Acquired for a research image collection, with no referral diagnosis — 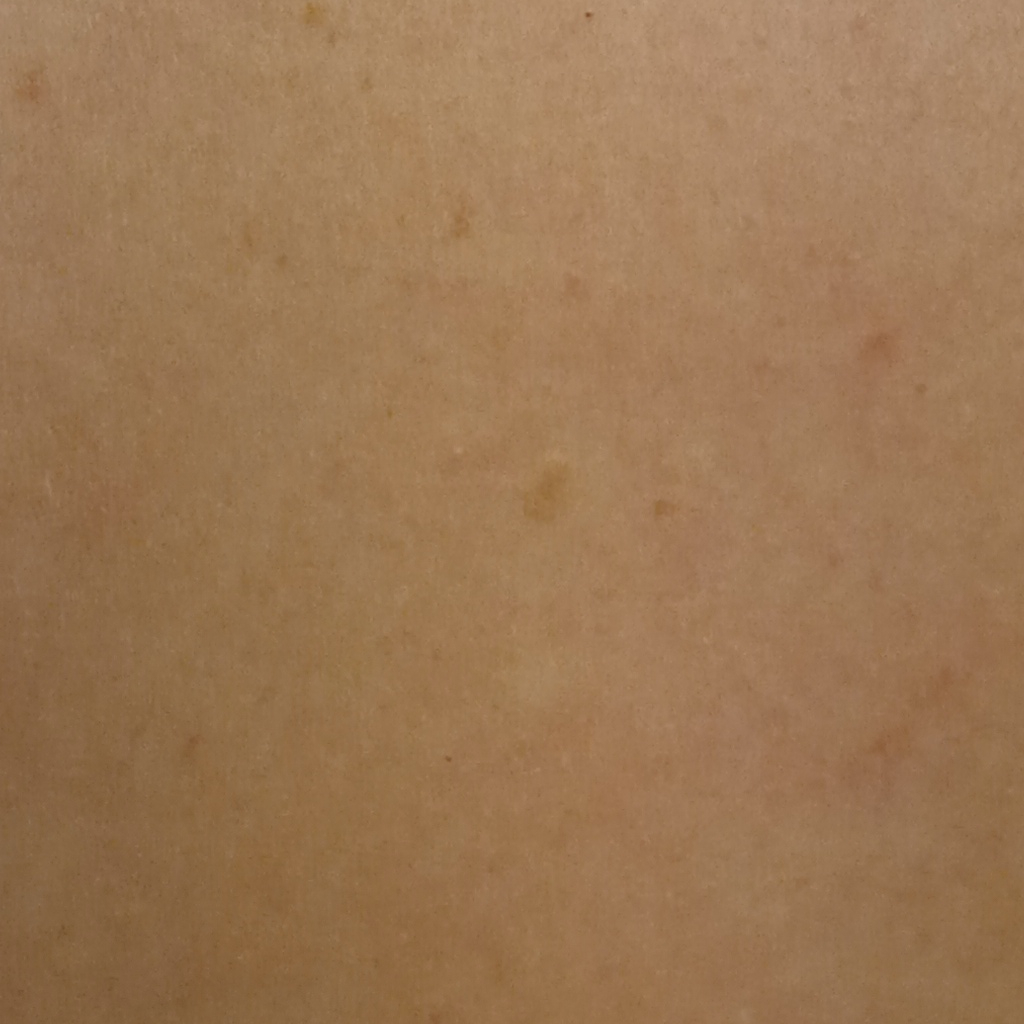The lesion is about 3.8 mm across.
The consensus diagnosis for this lesion was a seborrheic keratosis.